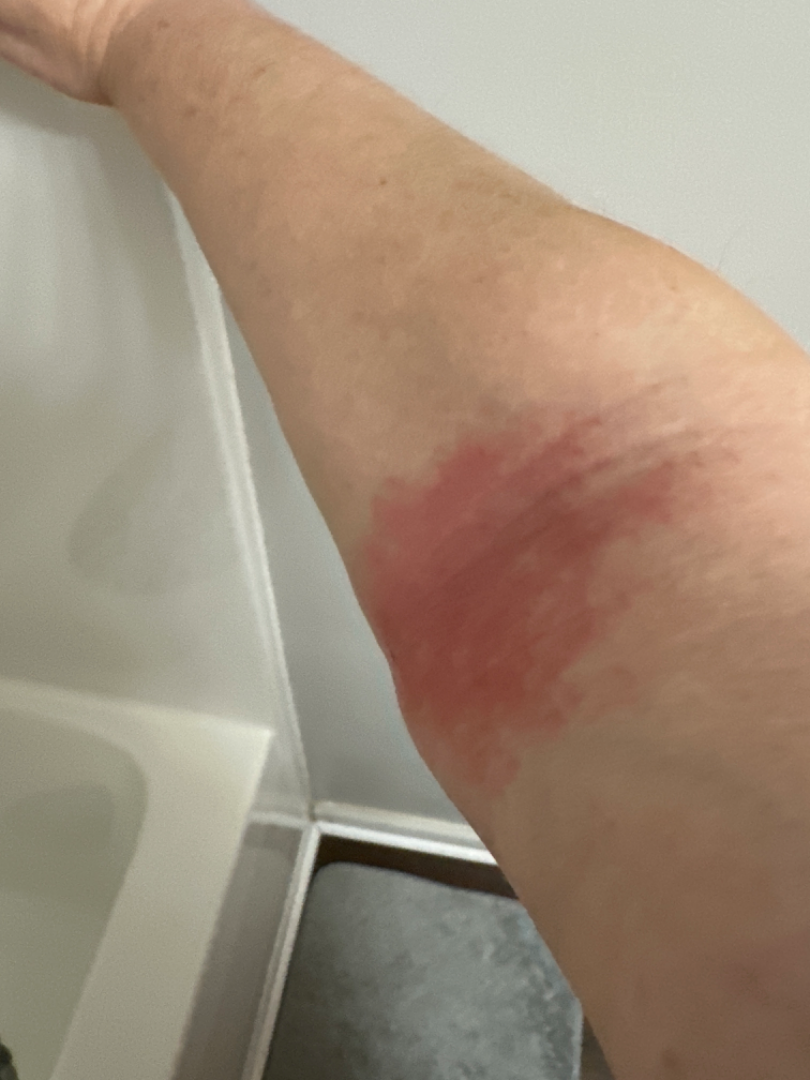| key | value |
|---|---|
| subject | female, age 40–49 |
| framing | at an angle |
| anatomic site | arm |
| differential diagnosis | Eczema (41%); Allergic Contact Dermatitis (41%); Psoriasis (18%) |